A dermatoscopic image of a skin lesion:
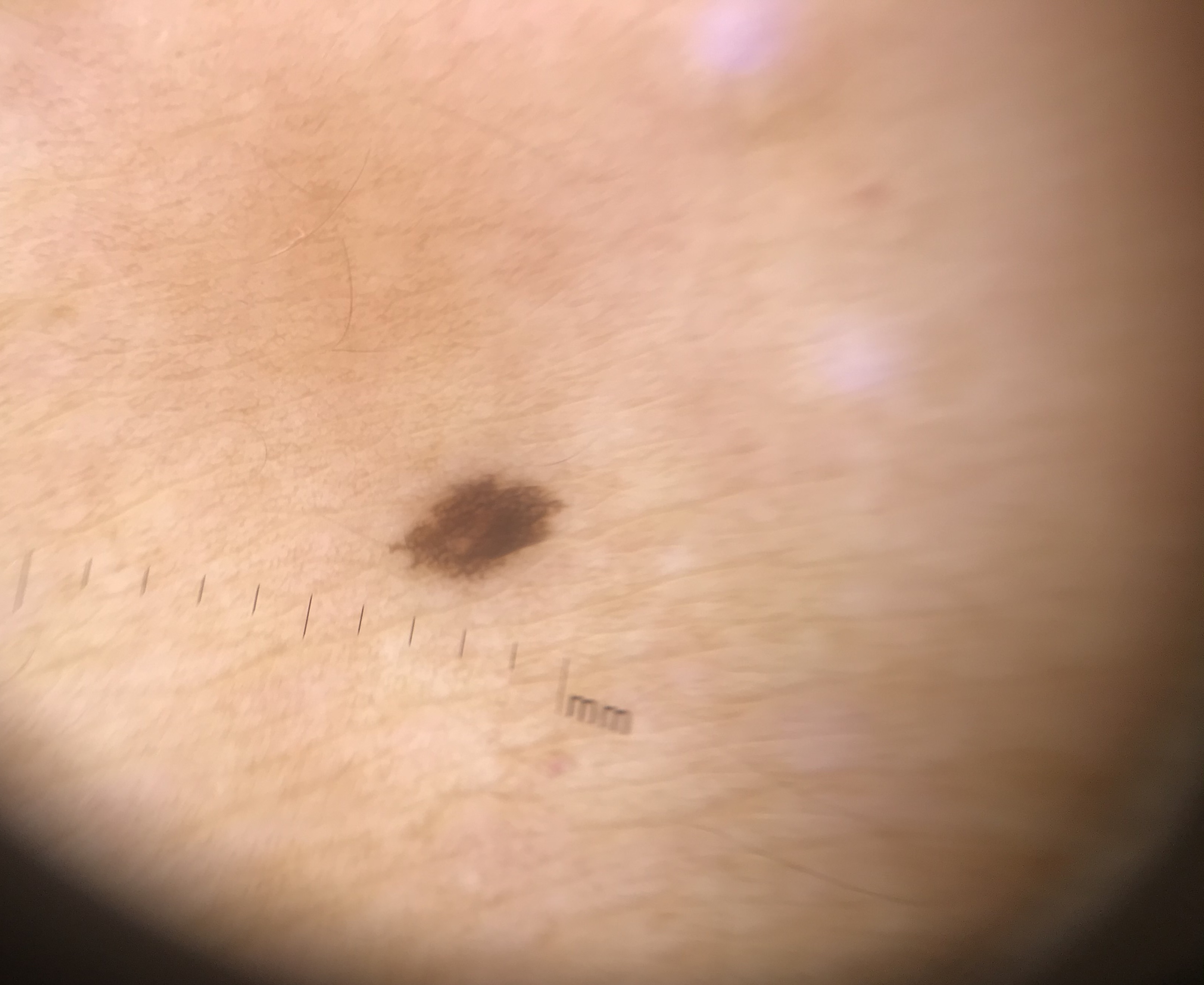Q: What was the diagnostic impression?
A: dysplastic junctional nevus (expert consensus)